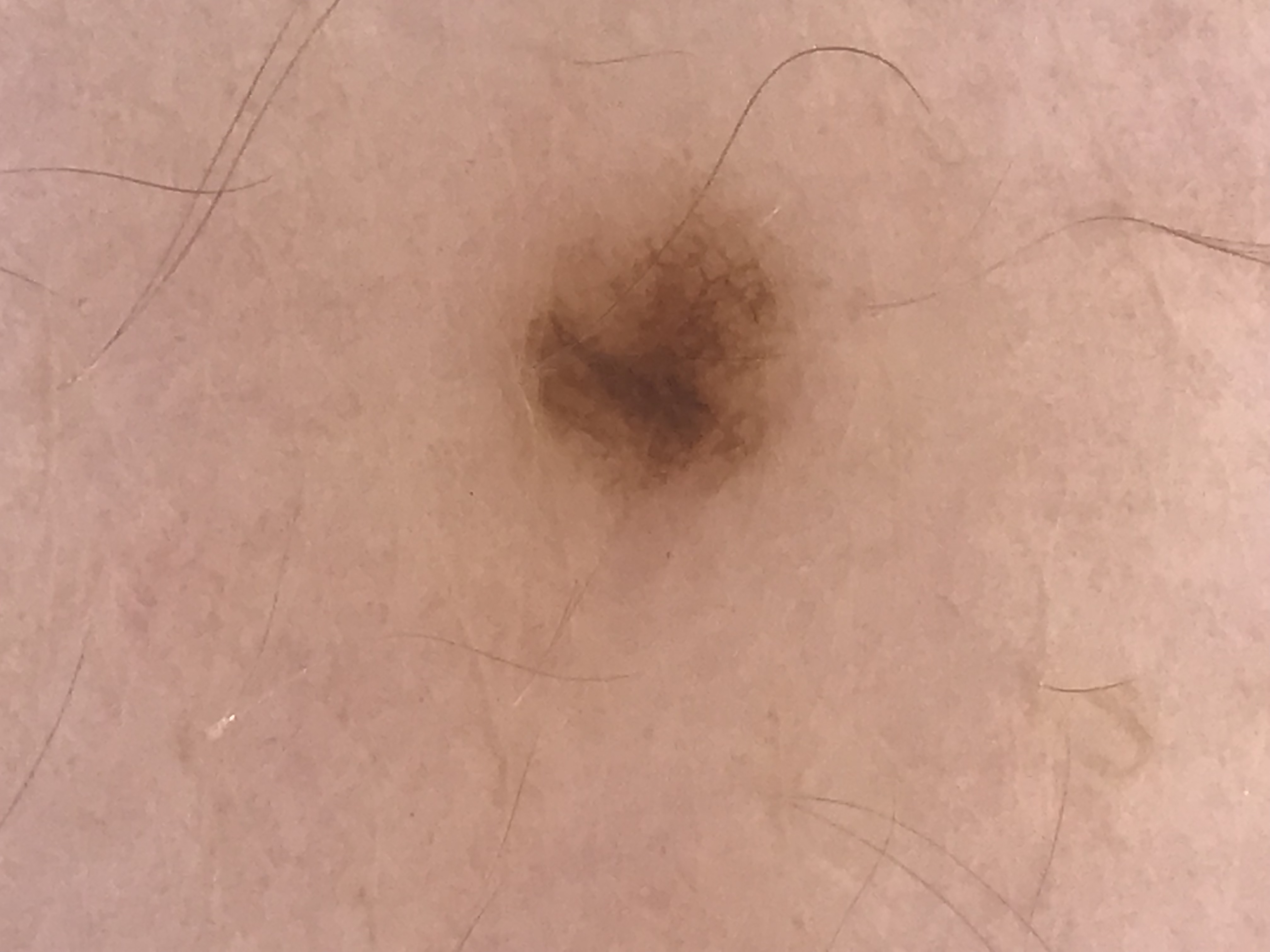• assessment: junctional nevus (expert consensus)